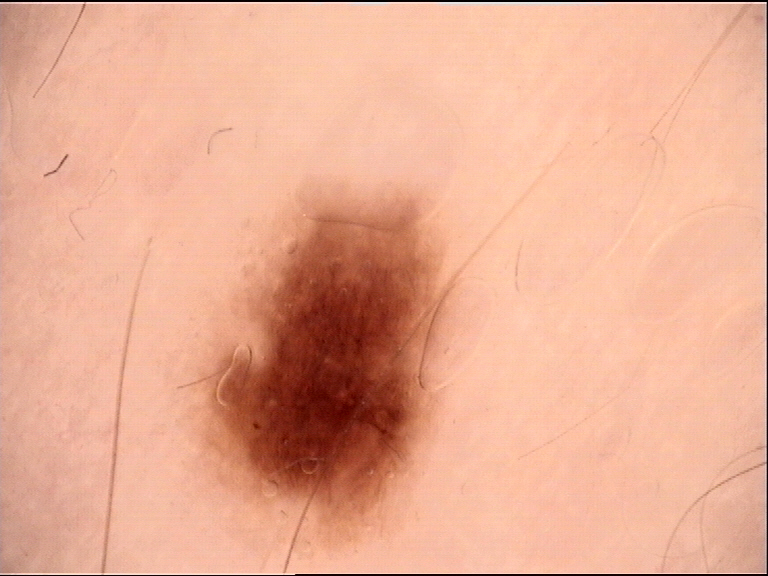modality: dermoscopy, subtype: banal, label: junctional nevus (expert consensus).